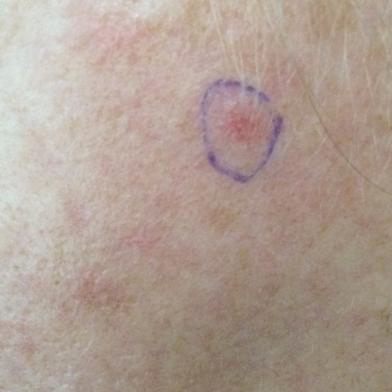modality=clinical photograph; assessment=actinic keratosis (clinical consensus).